Recorded as Fitzpatrick II · the chart notes prior malignancy (patient or family):
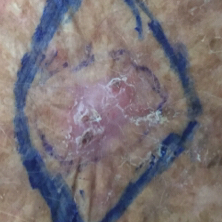Case:
• region · a forearm
• symptoms · pain, bleeding, itching, elevation / no growth, no change in appearance
• diagnosis · basal cell carcinoma (biopsy-proven)